A dermoscopic photograph of a skin lesion.
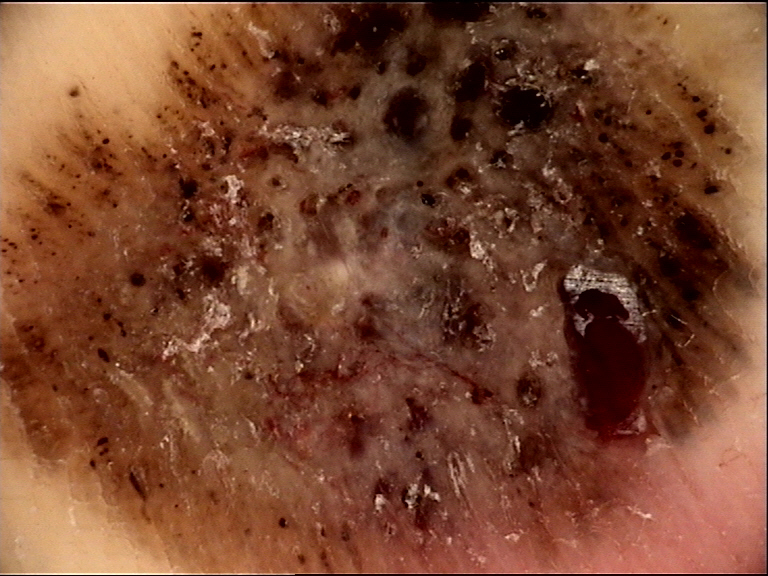Diagnosis: Histopathology confirmed a malignant lesion — an acral nodular melanoma.